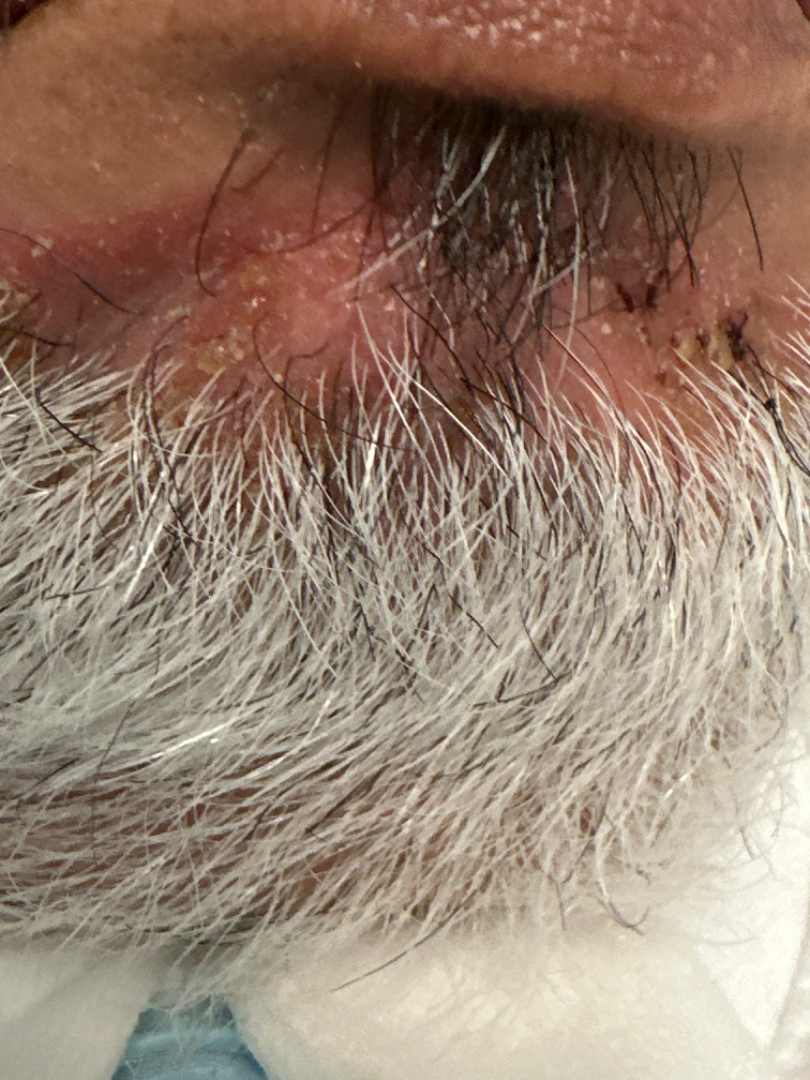Q: What is the framing?
A: close-up
Q: What is the dermatologist's impression?
A: a single dermatologist reviewed the case: the impression is Seborrheic Dermatitis